The patient says their skin tans without first burning; by self-report, a personal history of cancer and a personal history of skin cancer; a dermatoscopic image of a skin lesion; few moles overall by the patient's own estimate — 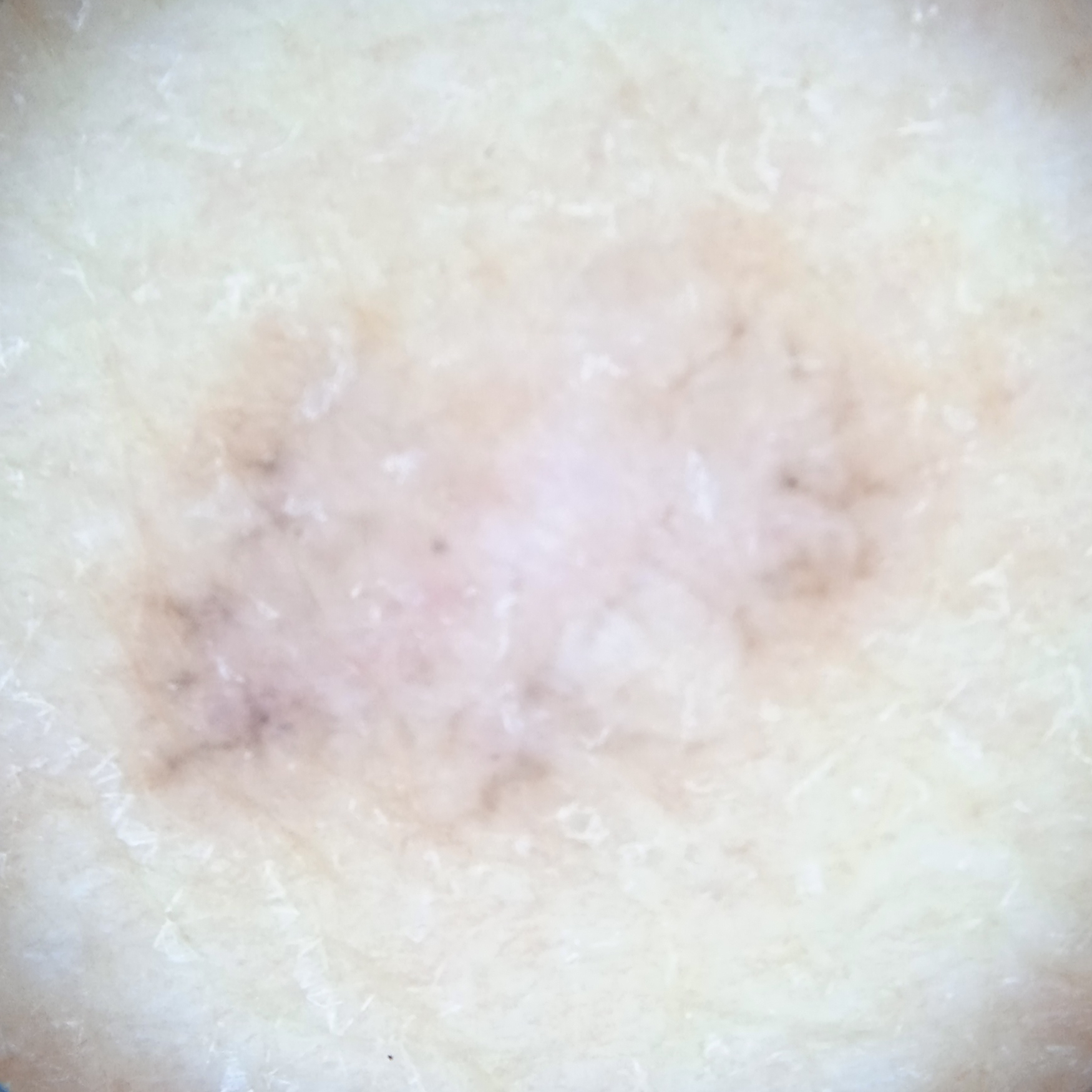| feature | finding |
|---|---|
| size | 10.4 mm |
| assessment | basal cell carcinoma (dermatologist consensus) |